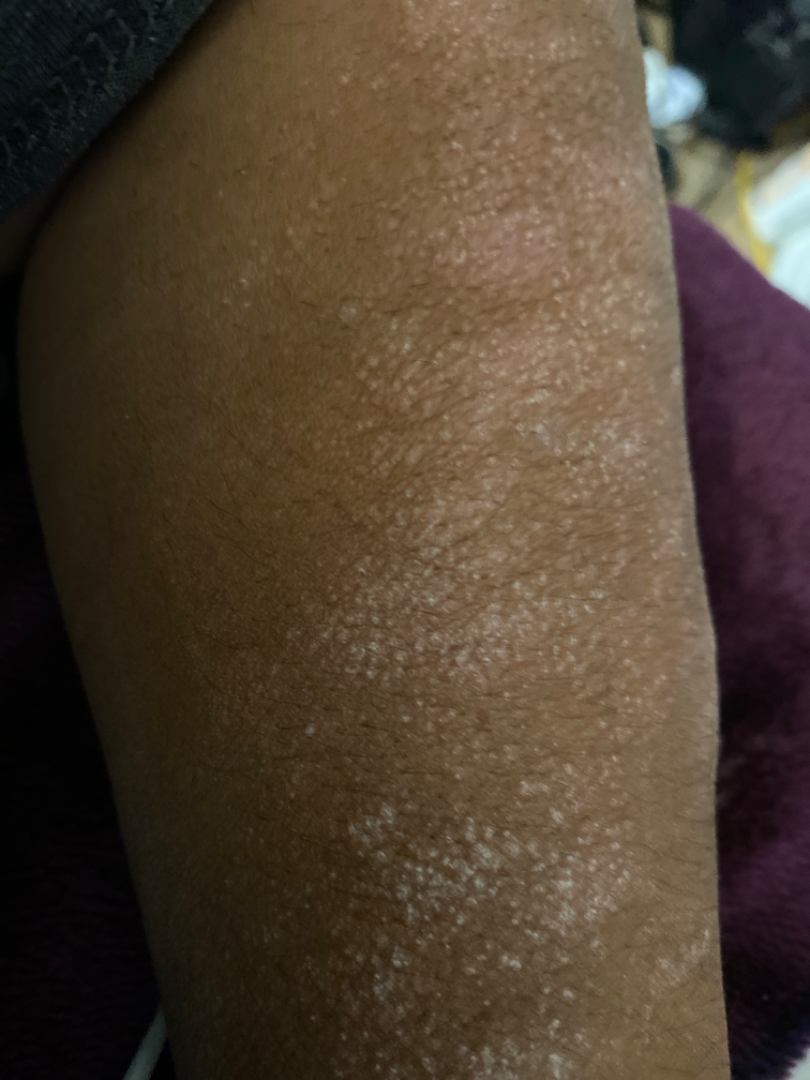| feature | finding |
|---|---|
| impression | most likely Eczema; also on the differential is Keratosis pilaris; possibly Lichen planus/lichenoid eruption |